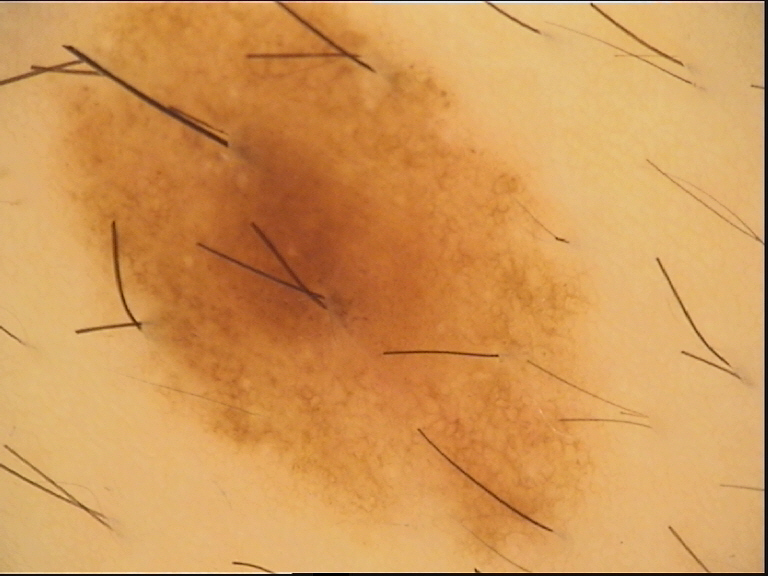A dermoscopic close-up of a skin lesion. Consistent with a benign lesion — a dysplastic junctional nevus.